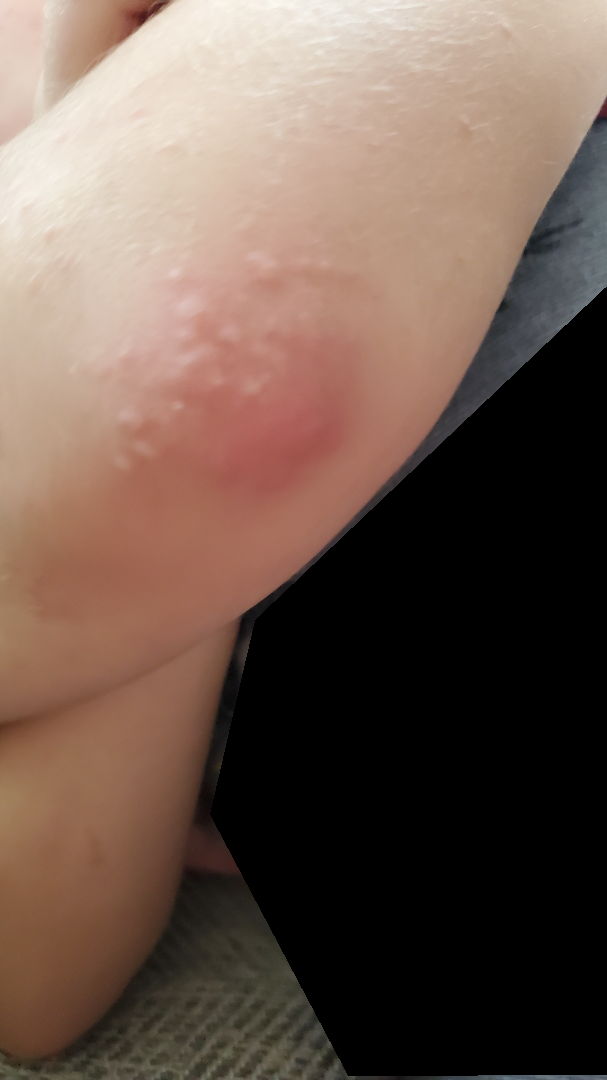Notes:
- assessment · indeterminate
- skin tone · lay graders estimated a Monk Skin Tone of 2
- view · close-up